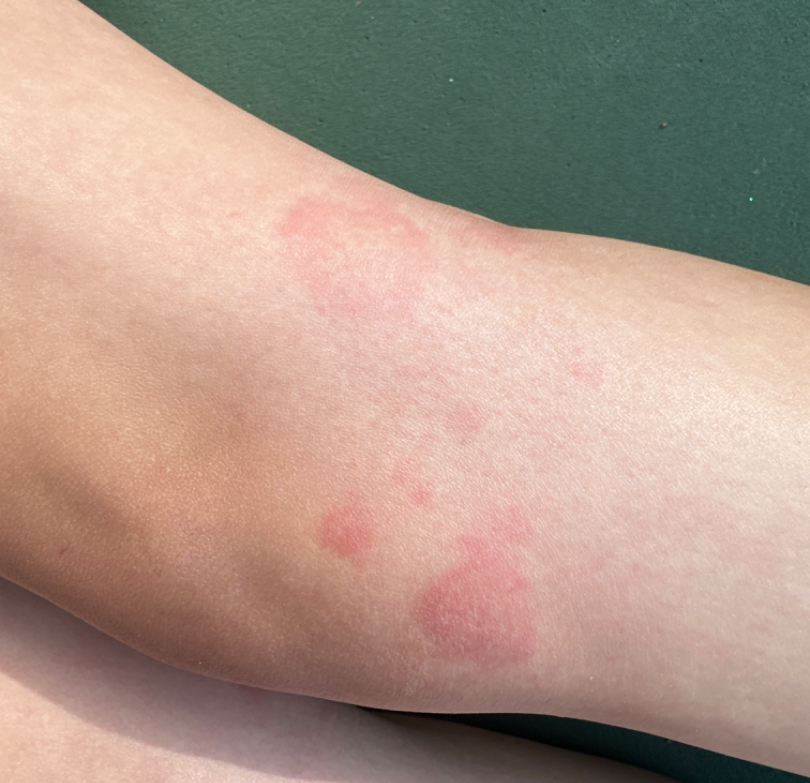On dermatologist assessment of the image, favoring Urticaria; possibly Eczema; an alternative is Granuloma annulare.